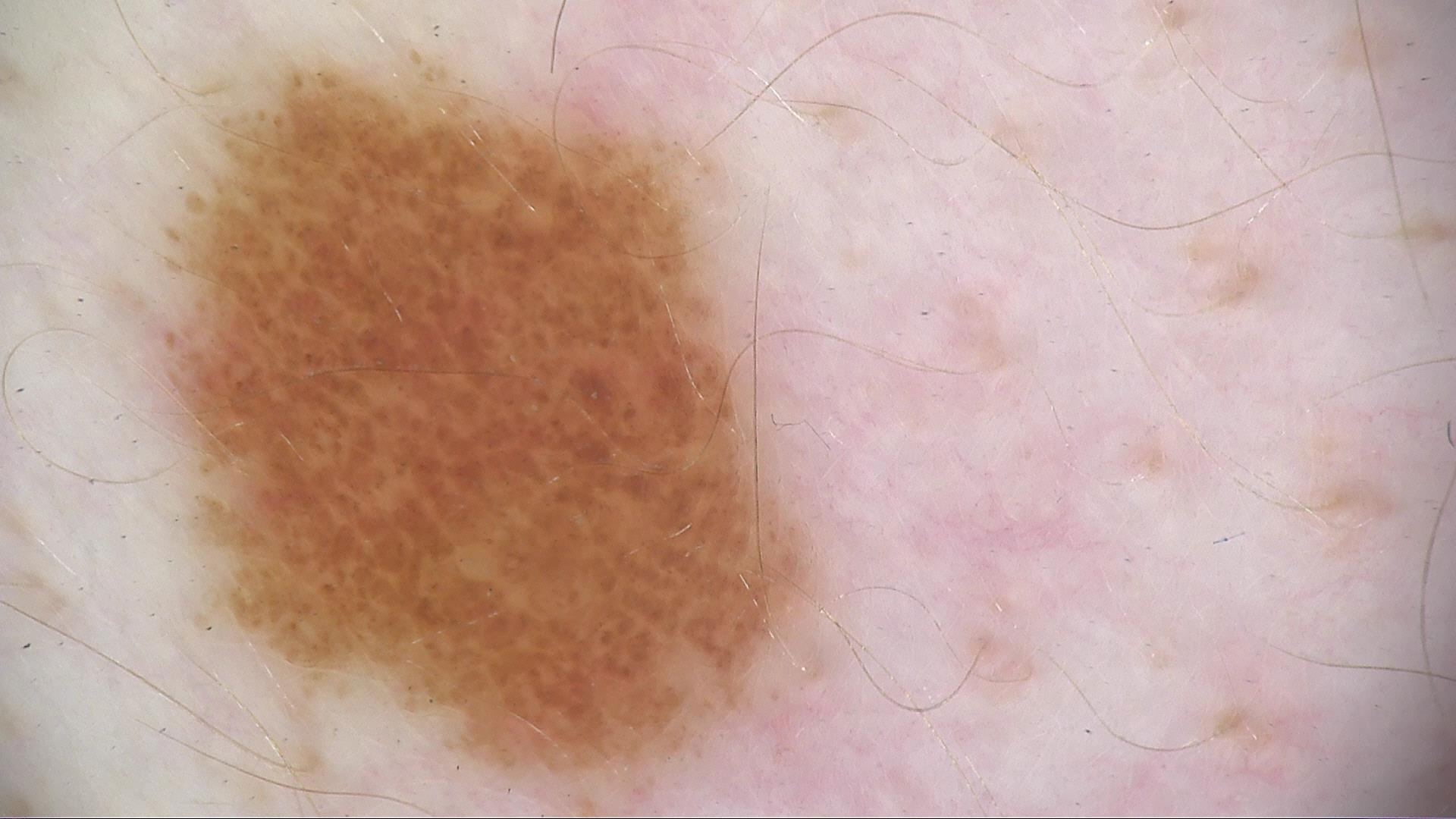Consistent with a dysplastic junctional nevus.